A clinical close-up photograph of a skin lesion · the patient was assessed as skin type II · a male subject in their 30s — 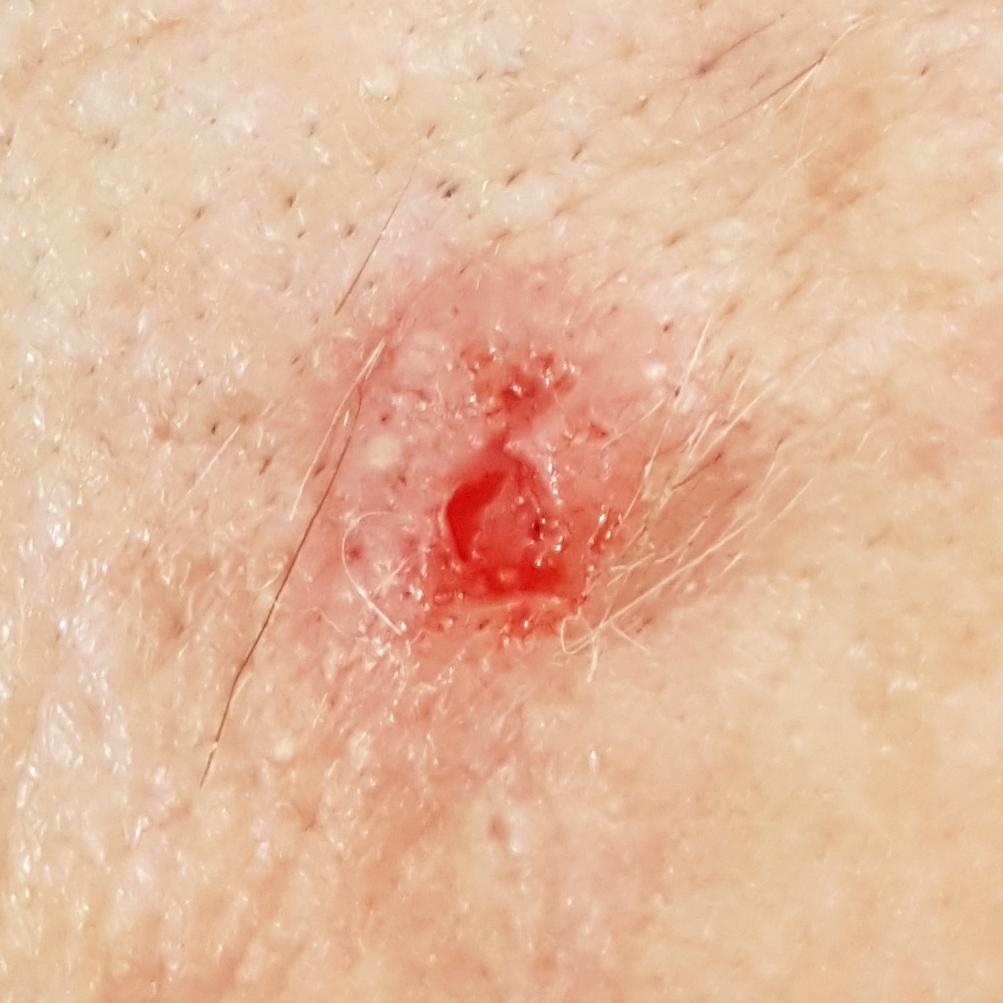The lesion is located on the face.
Confirmed on histopathology as a basal cell carcinoma.